A close-up photograph. The contributor is a female aged 18–29.
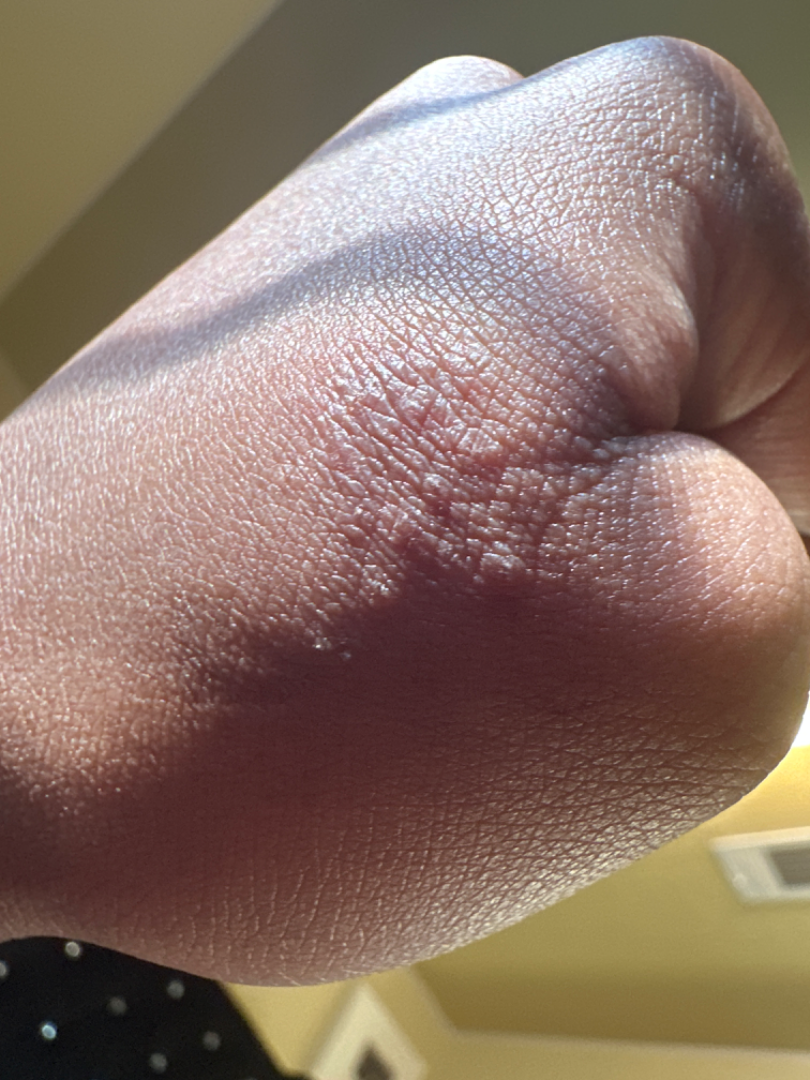On remote dermatologist review: the differential is split between Acute and chronic dermatitis, Allergic Contact Dermatitis and Irritant Contact Dermatitis.